A dermatoscopic image of a skin lesion.
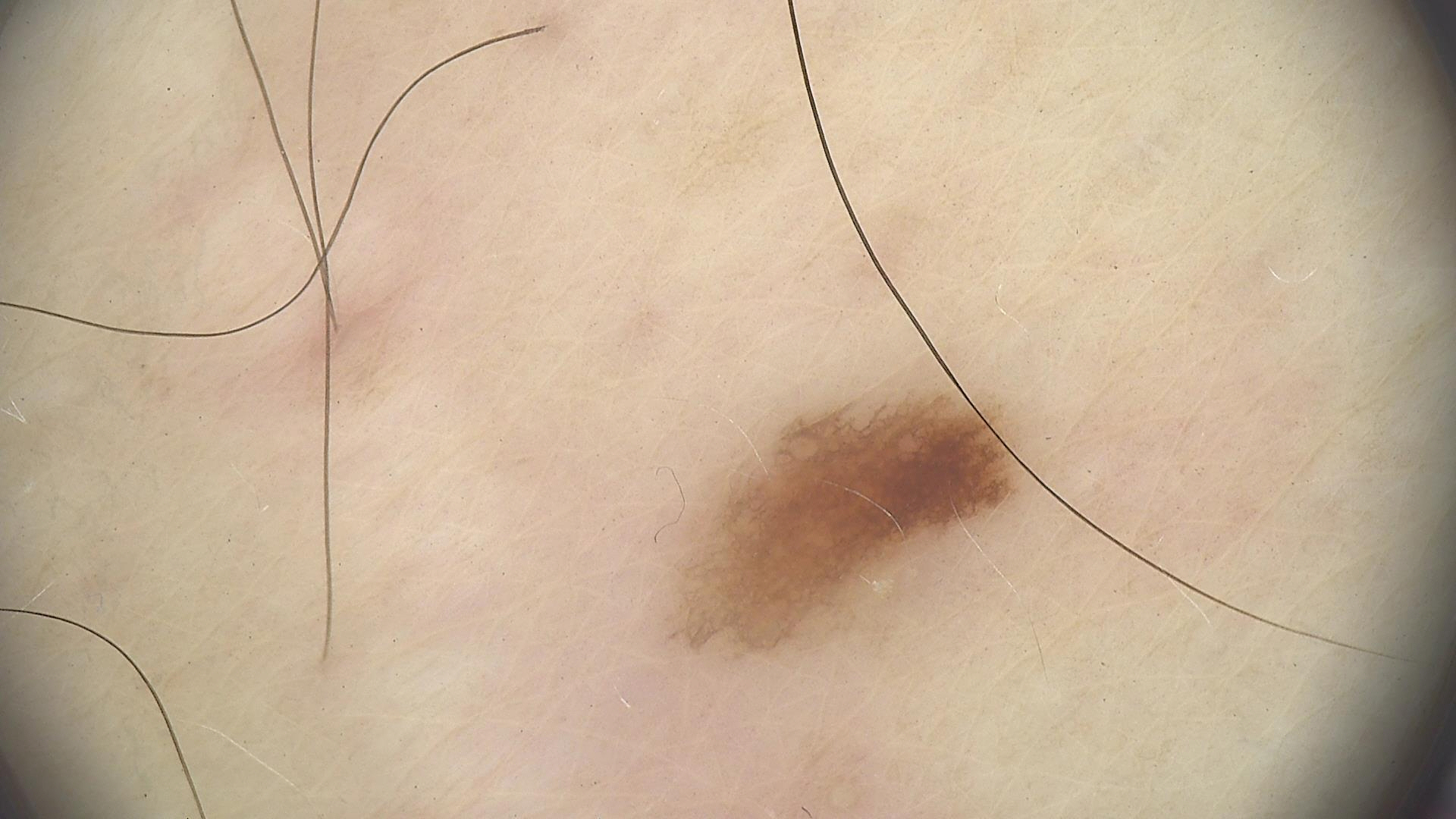class: dysplastic junctional nevus (expert consensus)